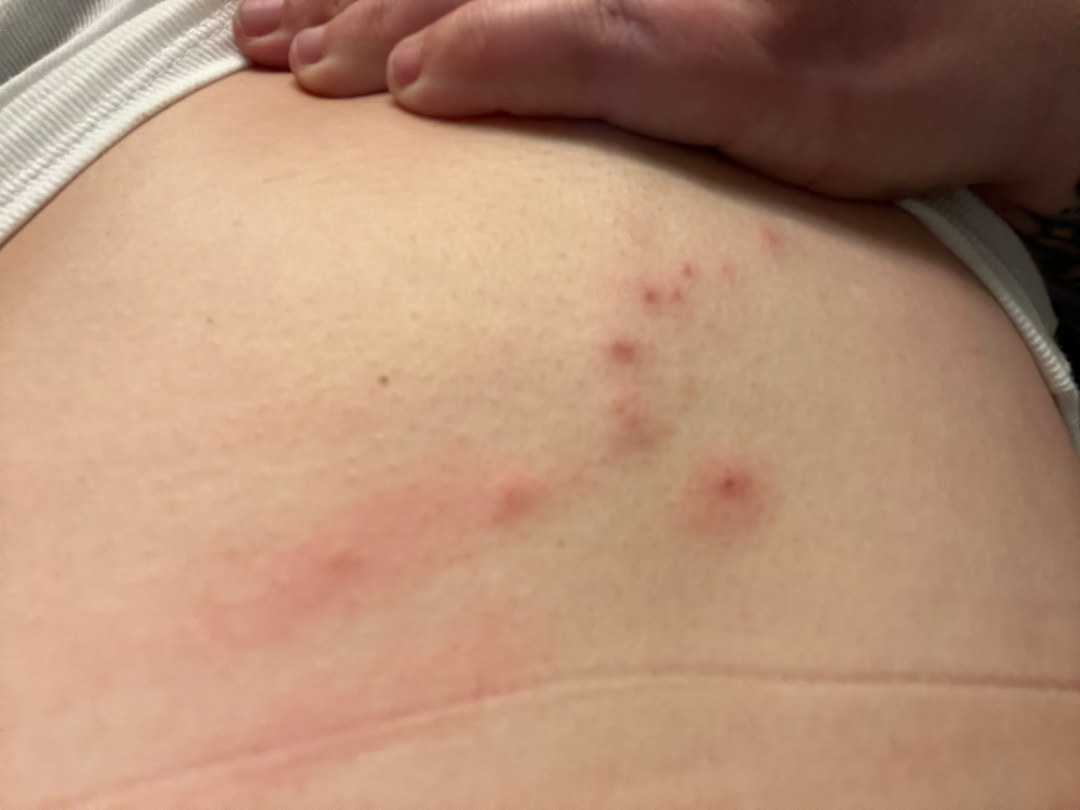- differential · Herpes Zoster (most likely)